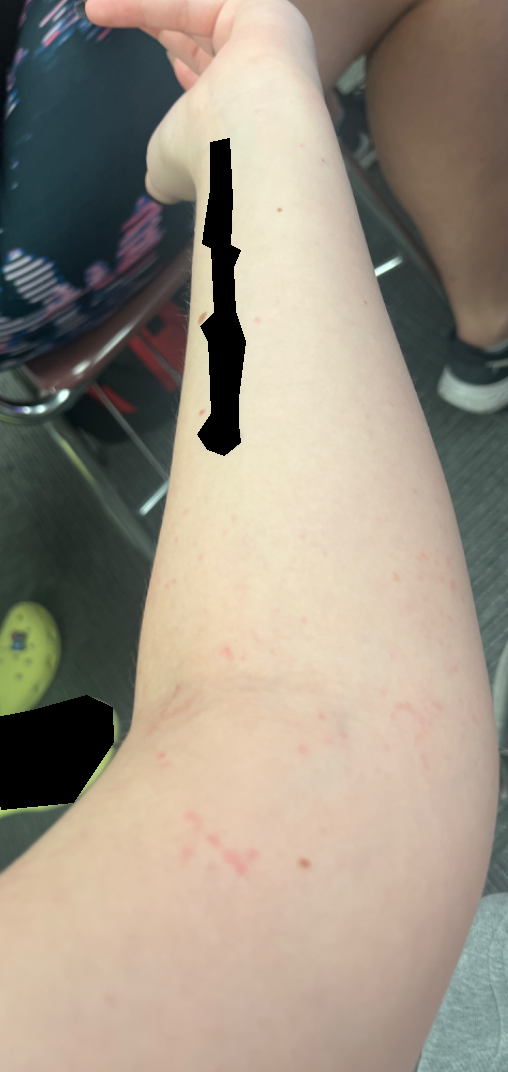| key | value |
|---|---|
| assessment | could not be assessed |
| shot type | at a distance |